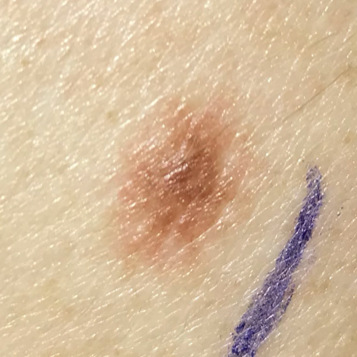patient = male, 36 years old
symptoms = itching
pathology = nevus (biopsy-proven)